A dermoscopic close-up of a skin lesion.
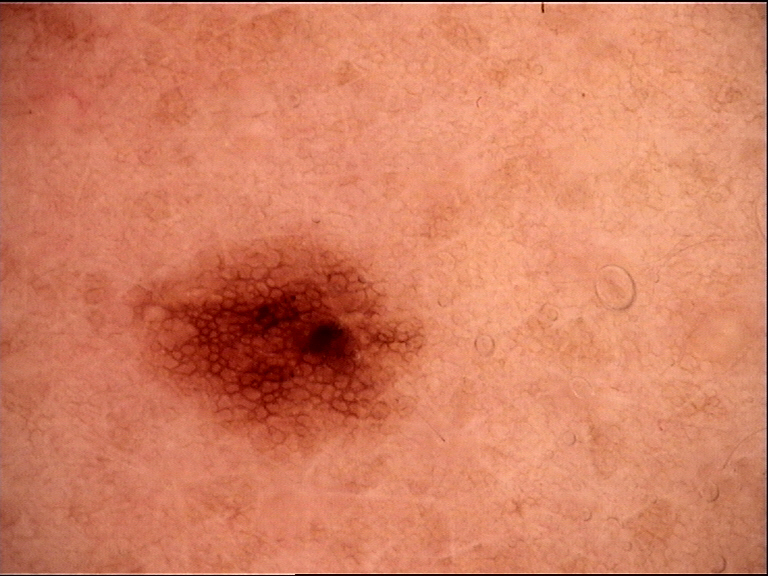The diagnostic label was a dysplastic junctional nevus.